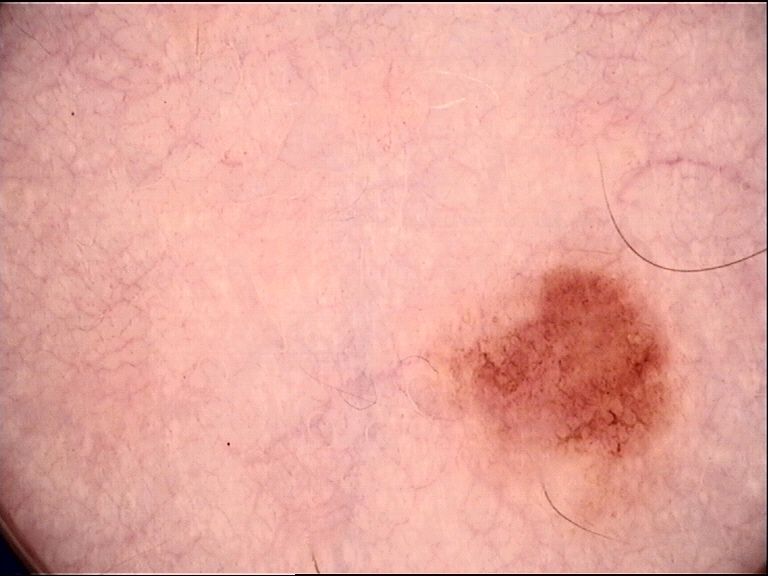diagnosis:
  name: junctional nevus
  code: jb
  malignancy: benign
  super_class: melanocytic
  confirmation: expert consensus